A female subject 78 years old · the patient says their skin tans without first burning · dermoscopy of a skin lesion · on a questionnaire the patient reported no immunosuppression · numerous moles by the patient's own estimate: 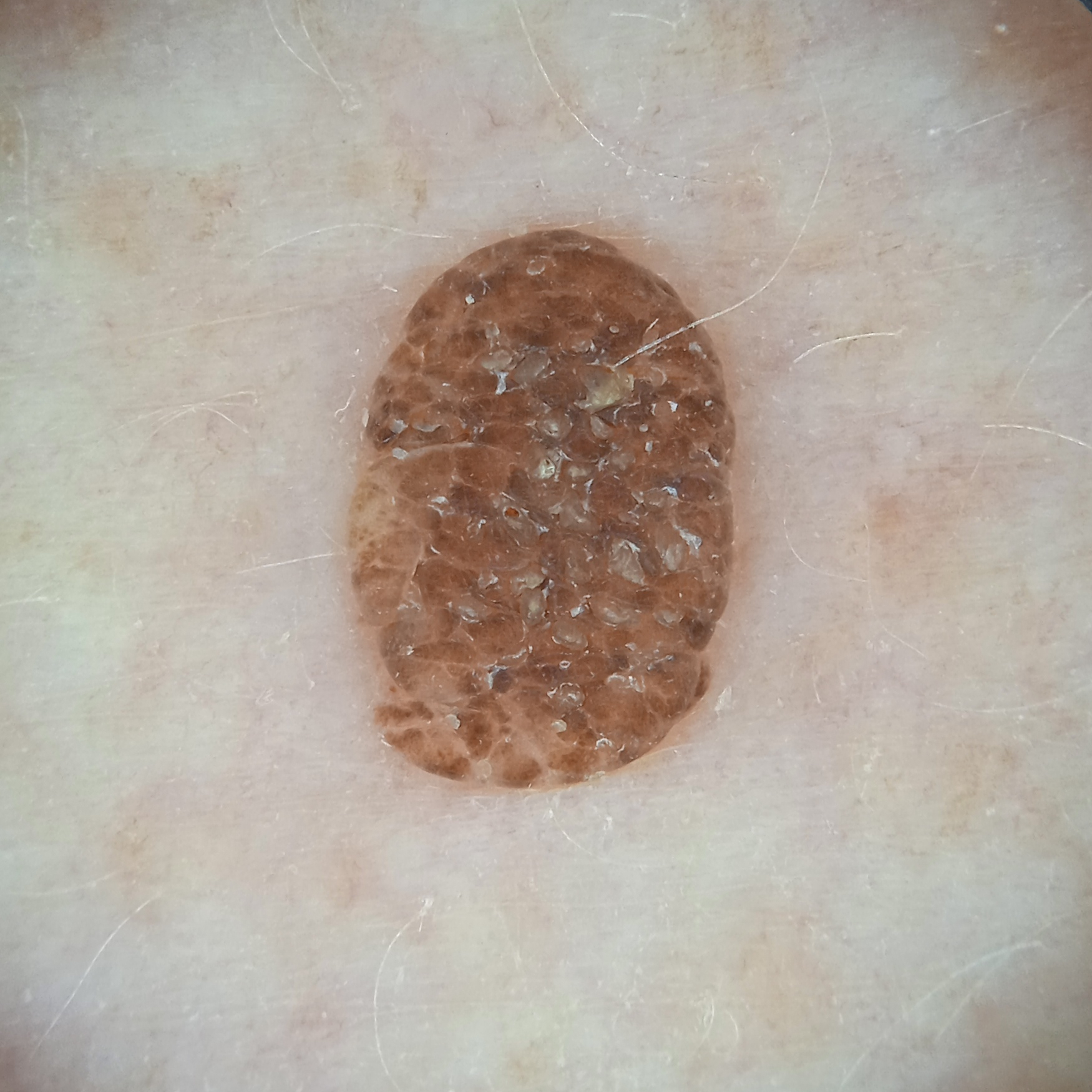Case:
– location · an arm
– lesion size · 5.6 mm
– diagnostic label · seborrheic keratosis (dermatologist consensus)